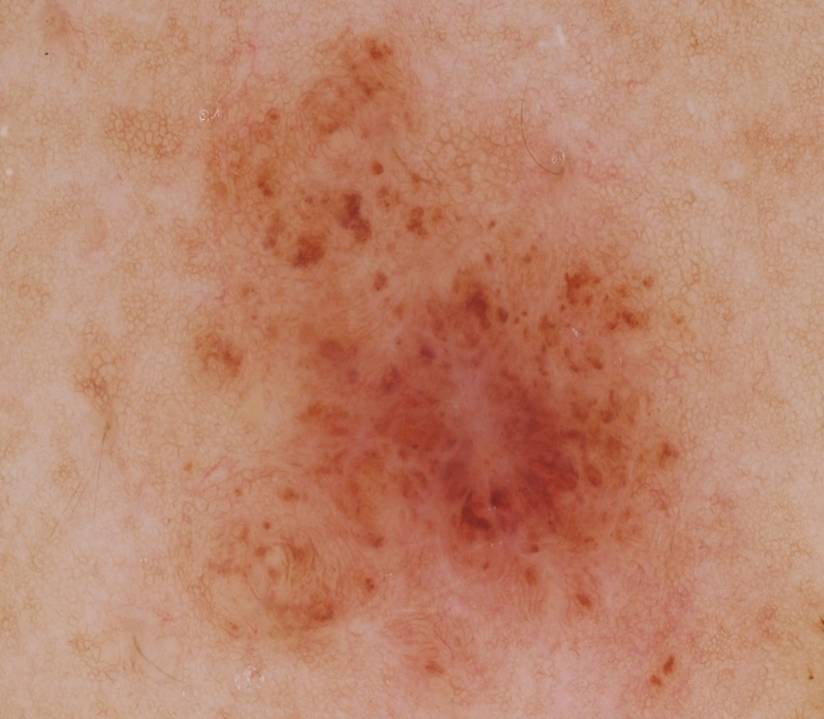Q: What kind of image is this?
A: dermoscopy of a skin lesion
Q: Which dermoscopic features were noted?
A: globules
Q: Where is the lesion in the image?
A: (193, 31, 692, 697)
Q: How much of the field does the lesion occupy?
A: ~38% of the field
Q: What did the assessment conclude?
A: a benign skin lesion